A dermoscopic image of a skin lesion.
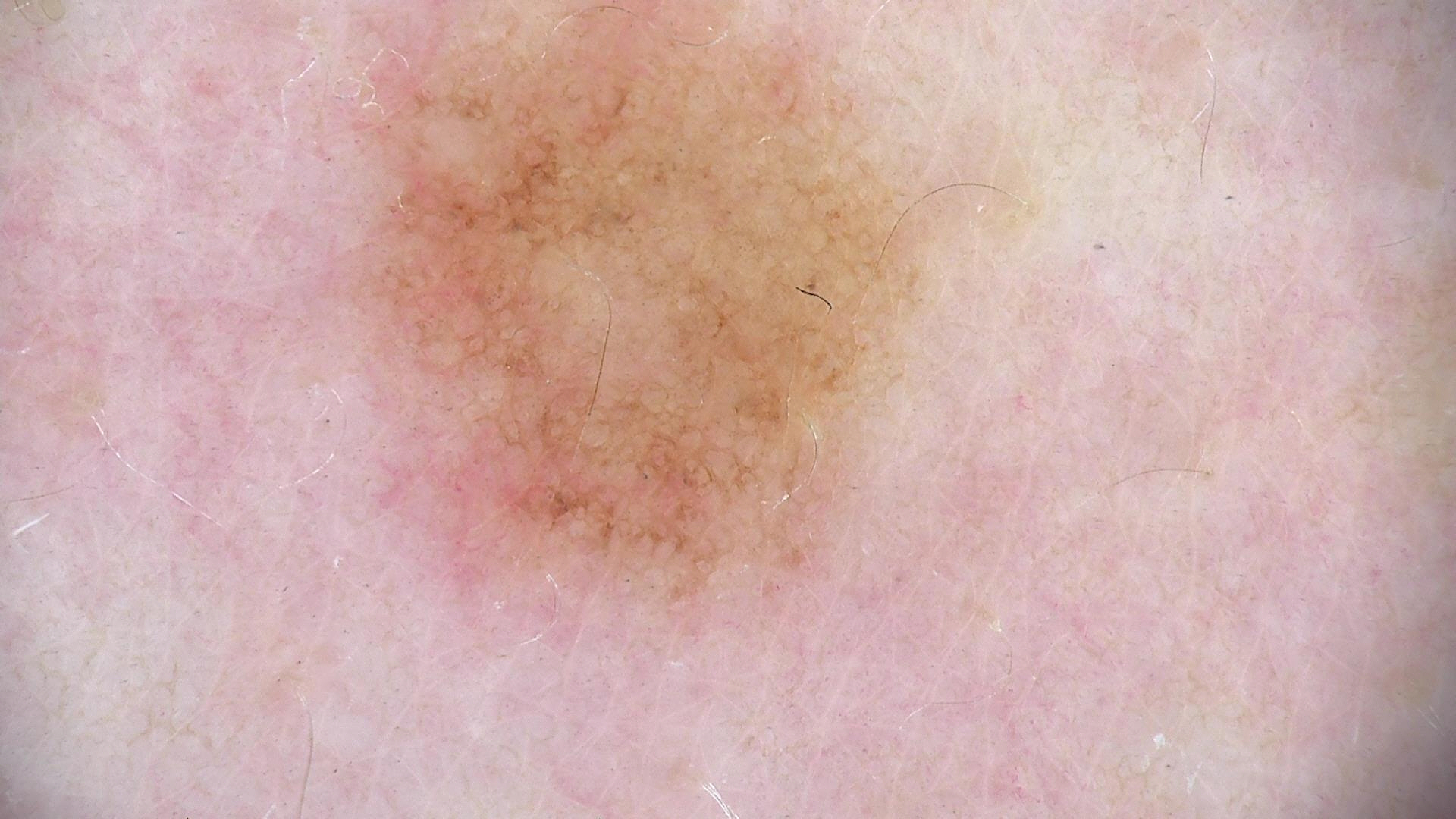class — dysplastic junctional nevus (expert consensus)